A dermoscopy image of a single skin lesion:
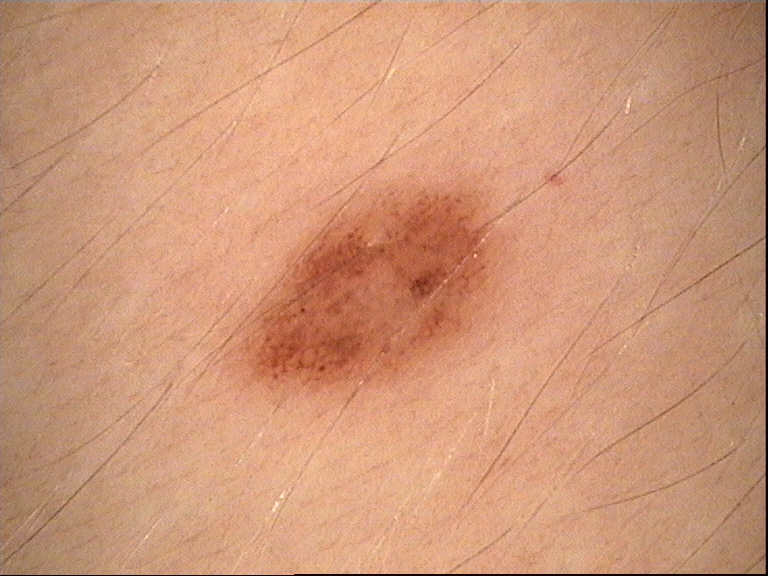{"diagnosis": {"name": "dysplastic compound nevus", "code": "cd", "malignancy": "benign", "super_class": "melanocytic", "confirmation": "expert consensus"}}